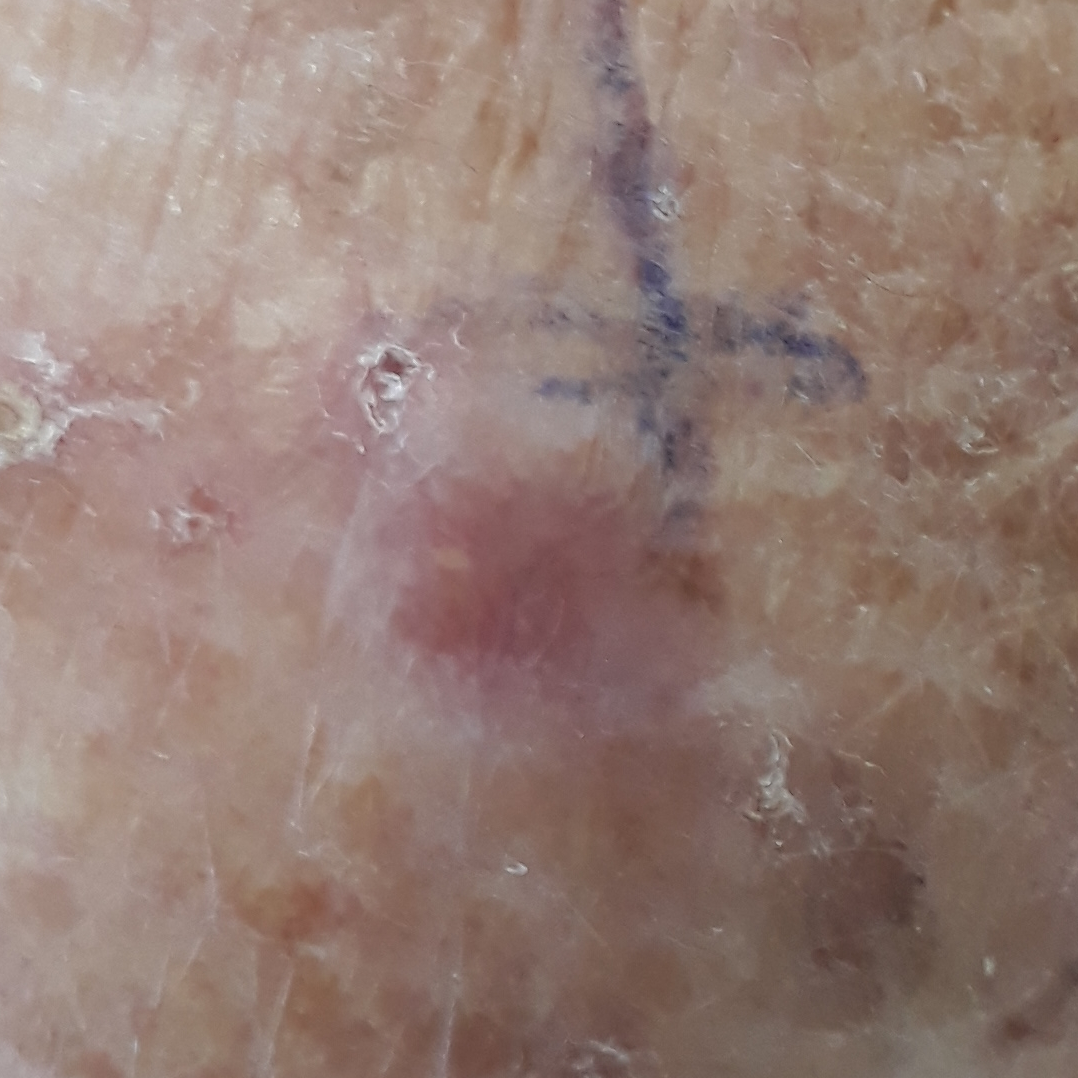Case summary:
A female patient age 61. A smartphone photograph of a skin lesion. History notes pesticide exposure, no prior skin cancer (patient or family), and no prior malignancy (patient or family). Fitzpatrick phototype III. Located on a hand. The lesion measures 4 × 3 mm. By the patient's account, the lesion itches and is elevated.
Pathology:
Biopsy-confirmed as a malignant lesion — a basal cell carcinoma.